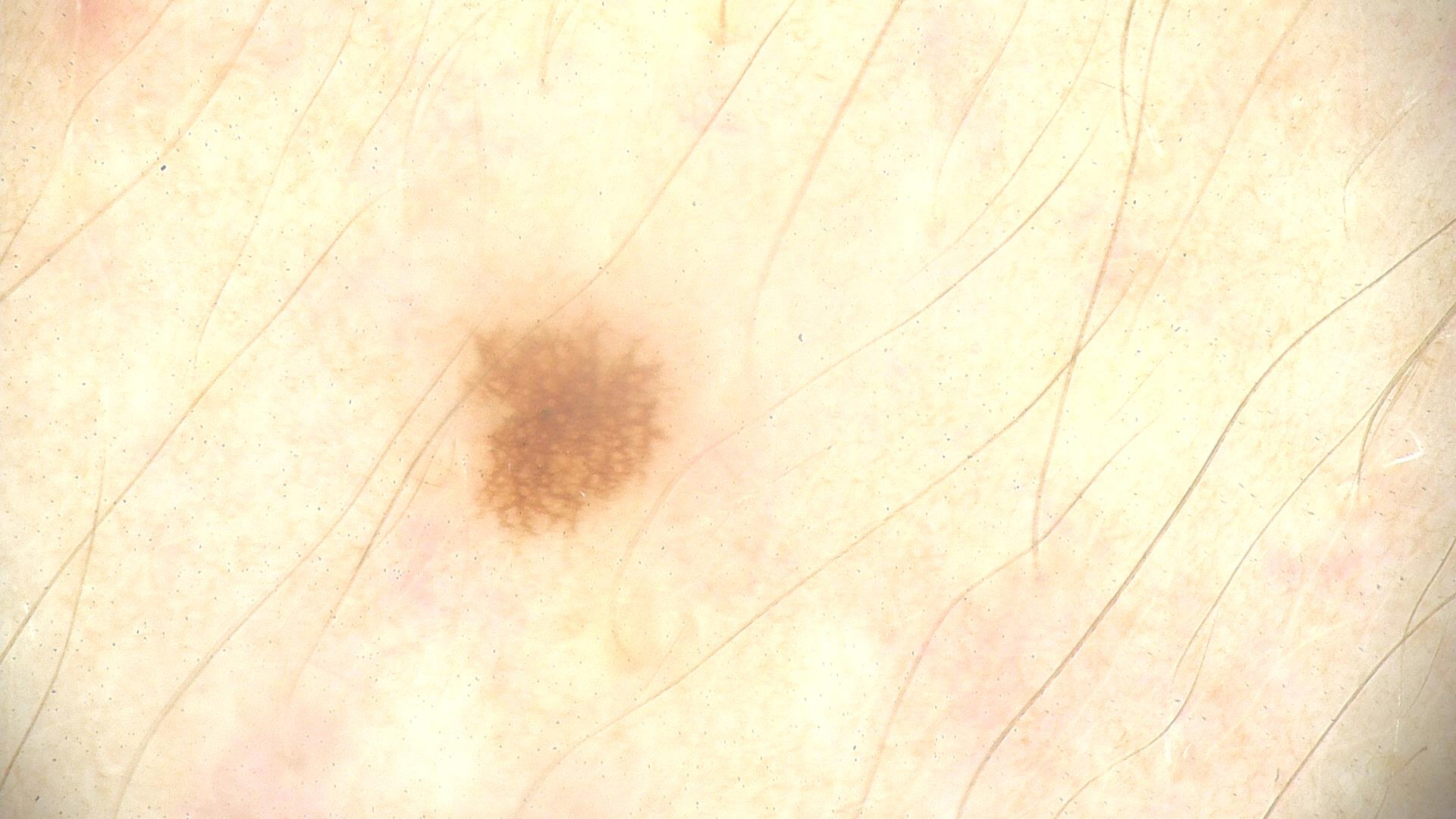A dermoscopic photograph of a skin lesion. Classified as a benign lesion — a dysplastic junctional nevus.